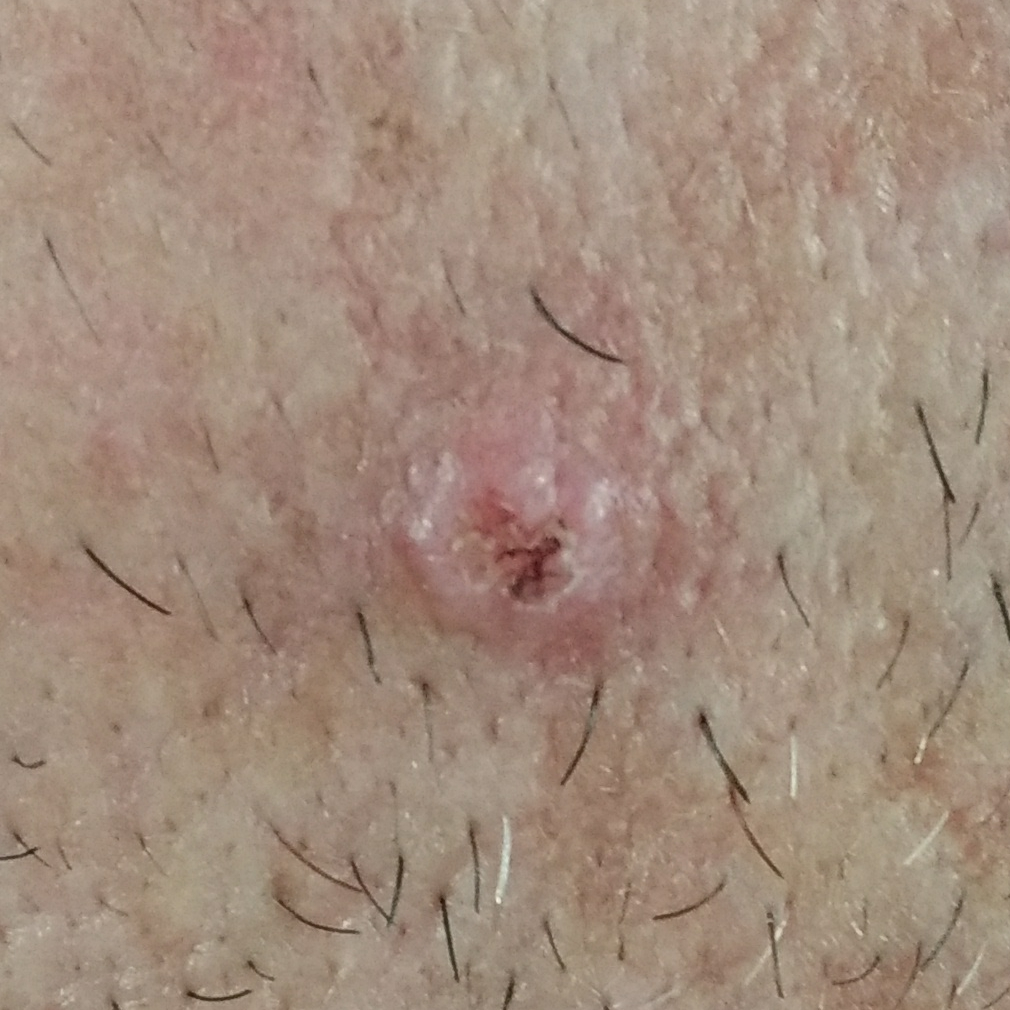FST: II
exposure history: no pesticide exposure, no prior skin cancer (patient or family)
image type: clinical photograph
patient: male, 53 years of age
location: the face
diameter: 7x5 mm
reported symptoms: pain, bleeding, growth, elevation, itching / no change in appearance
pathology: actinic keratosis (biopsy-proven)